A dermatoscopic image of a skin lesion:
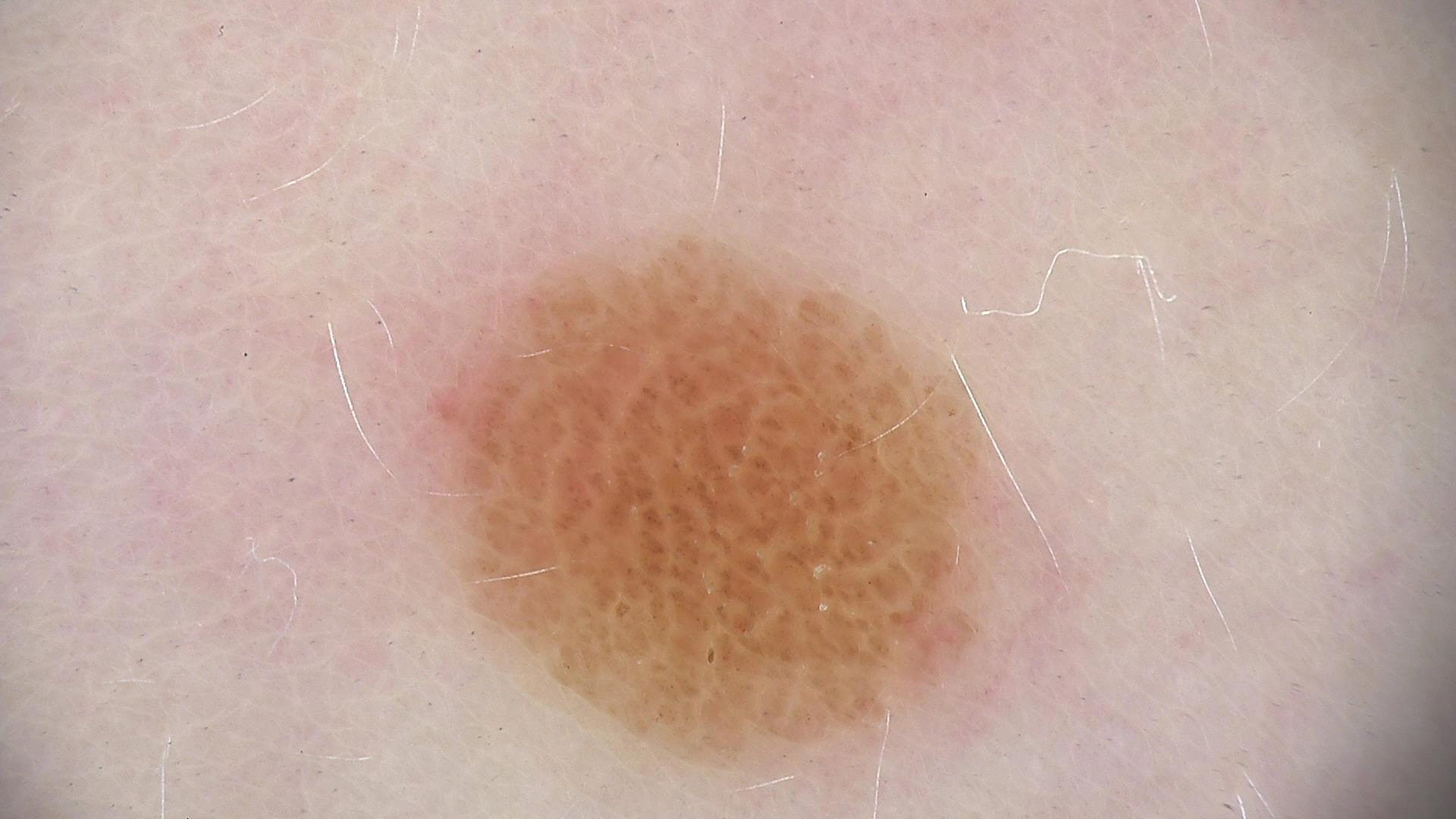Diagnosed as a dysplastic compound nevus.